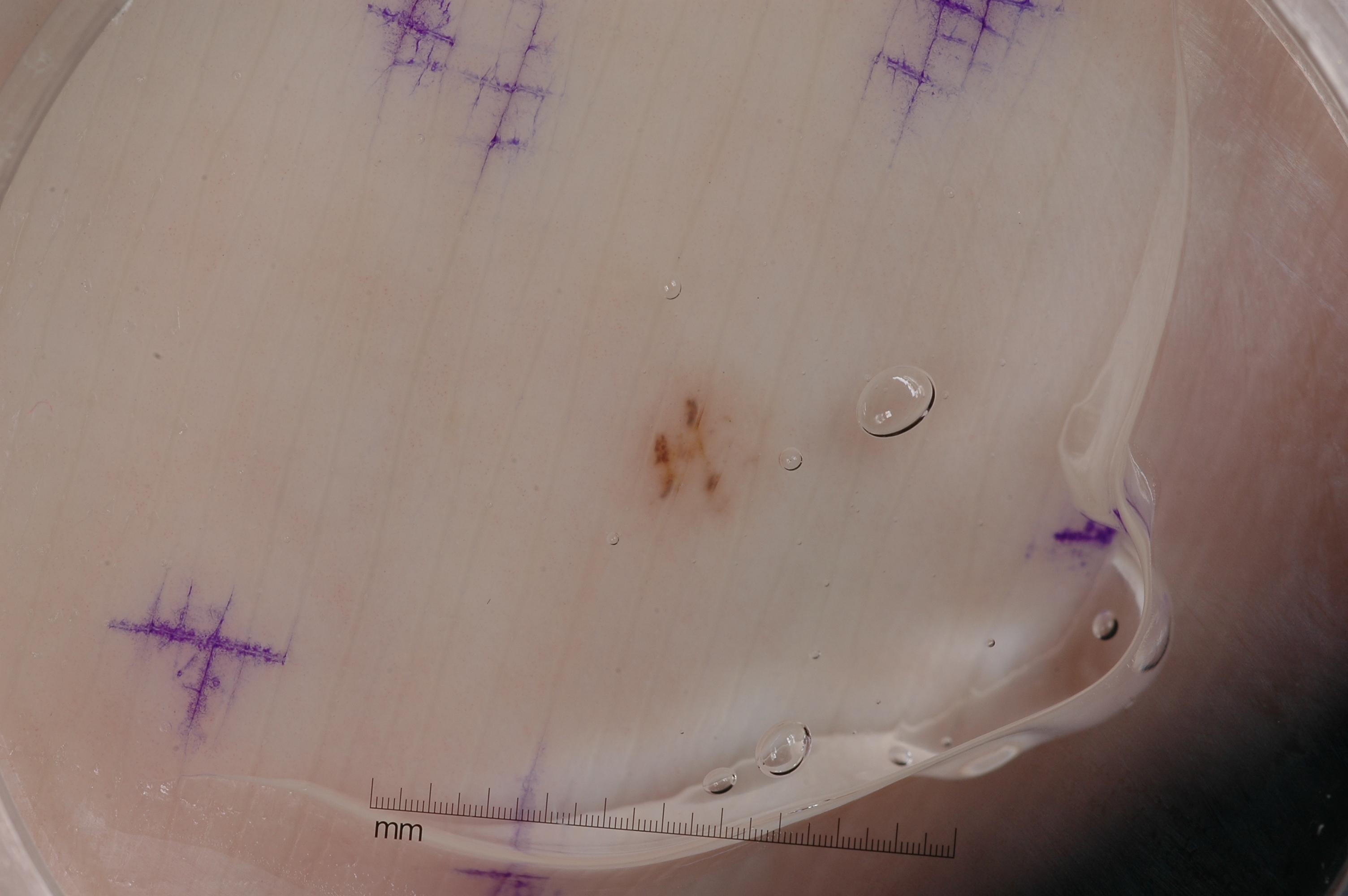Case summary:
A dermatoscopic image of a skin lesion. On dermoscopy, the lesion shows no streaks, milia-like cysts, pigment network, or negative network. In (x1, y1, x2, y2) order, the lesion is located at bbox(626, 370, 771, 545).
Conclusion:
The lesion was assessed as a melanocytic nevus, a benign lesion.